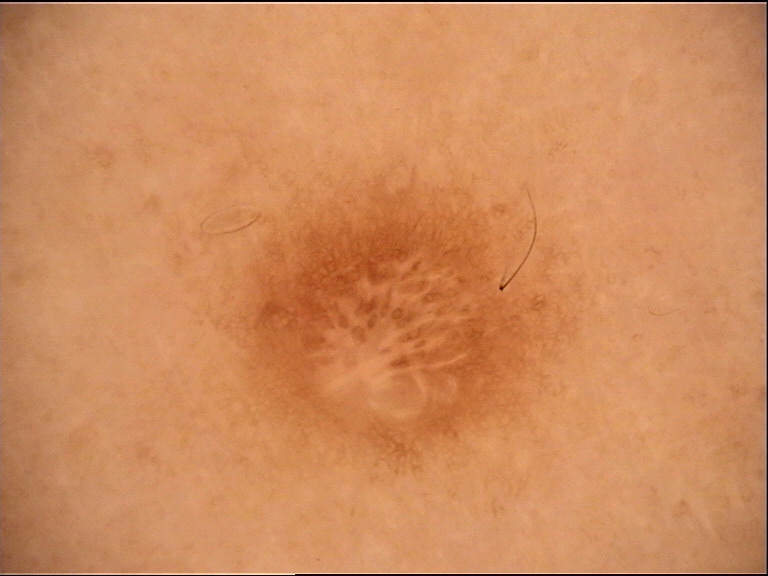• image type: dermoscopy
• category: fibro-histiocytic
• diagnosis: dermatofibroma (expert consensus)